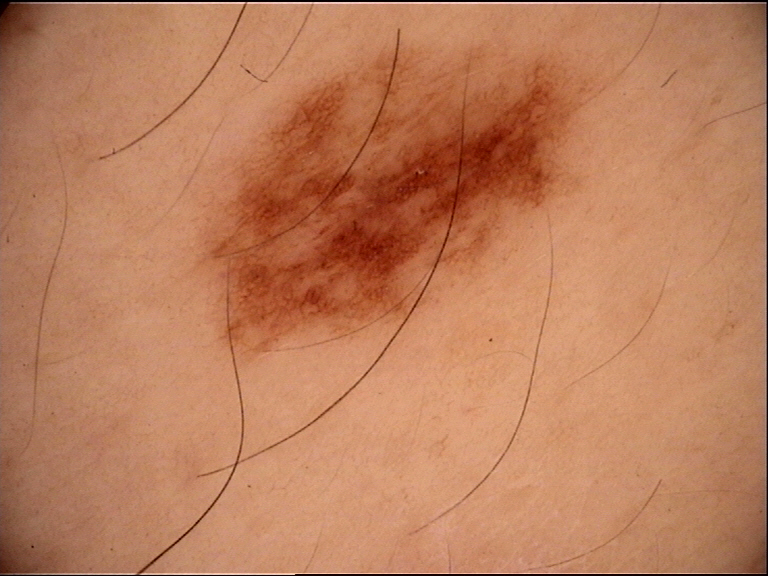Findings:
– imaging: dermoscopy
– assessment: dysplastic junctional nevus (expert consensus)